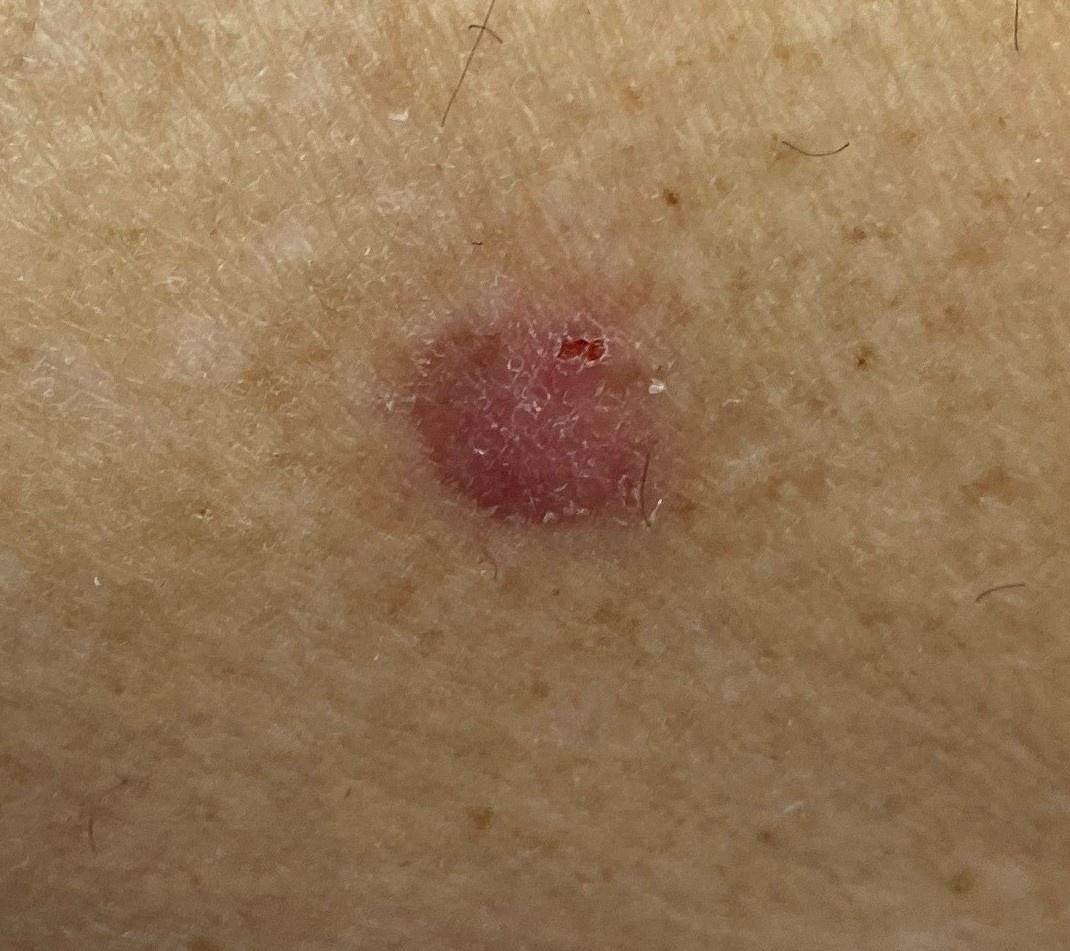Findings: A female subject aged 58 to 62. The lesion is located on a lower extremity. Pathology: Biopsy-confirmed as a malignant, adnexal lesion — a basal cell carcinoma.